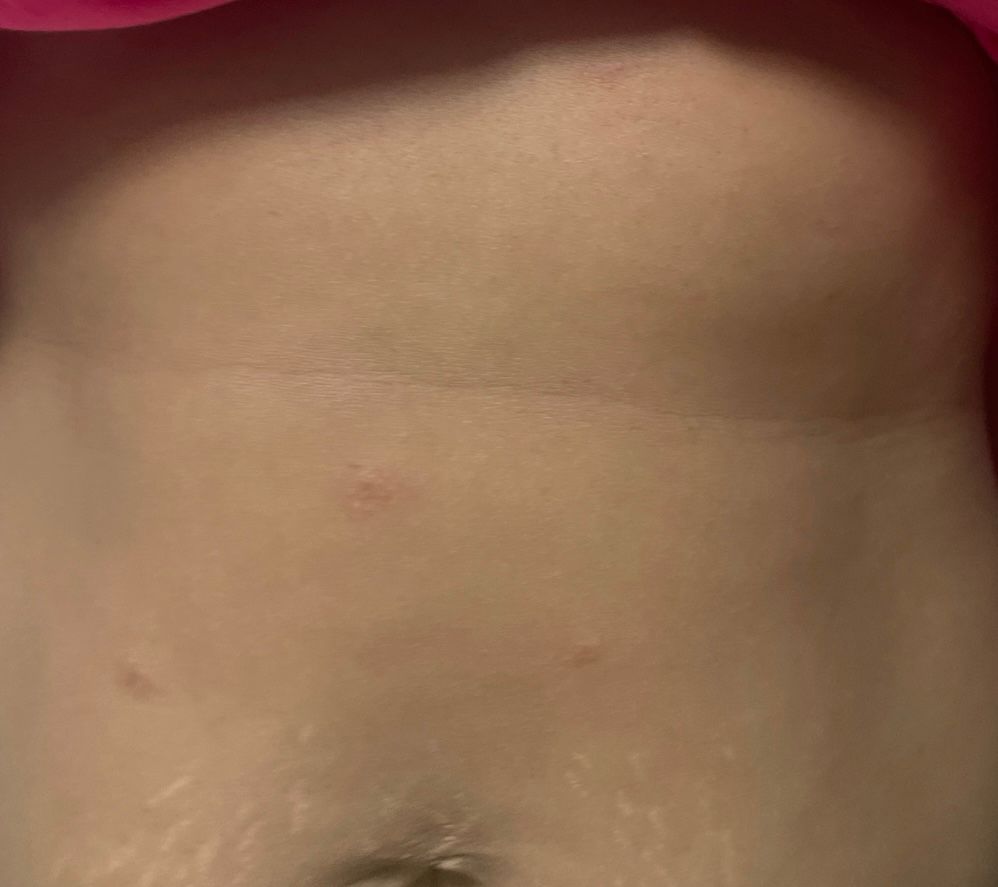The reviewing dermatologist was unable to assign a differential diagnosis from the image.